The patient indicates itching. The photograph was taken at an angle. Skin tone: Fitzpatrick phototype III; non-clinician graders estimated 2 on the Monk Skin Tone. The patient indicates the lesion is raised or bumpy. Self-categorized by the patient as a rash. The condition has been present for one to three months. The subject is a male aged 70–79. The lesion involves the leg — 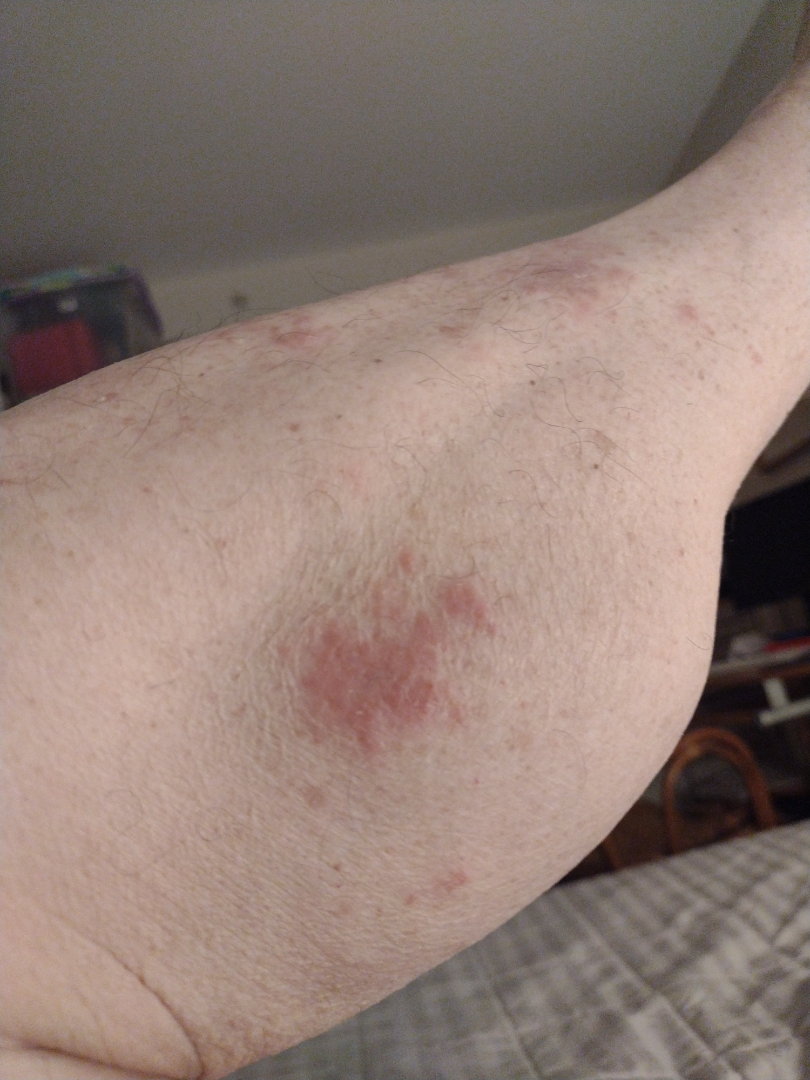The reviewer was unable to grade this case for skin condition.